A dermoscopic image of a skin lesion.
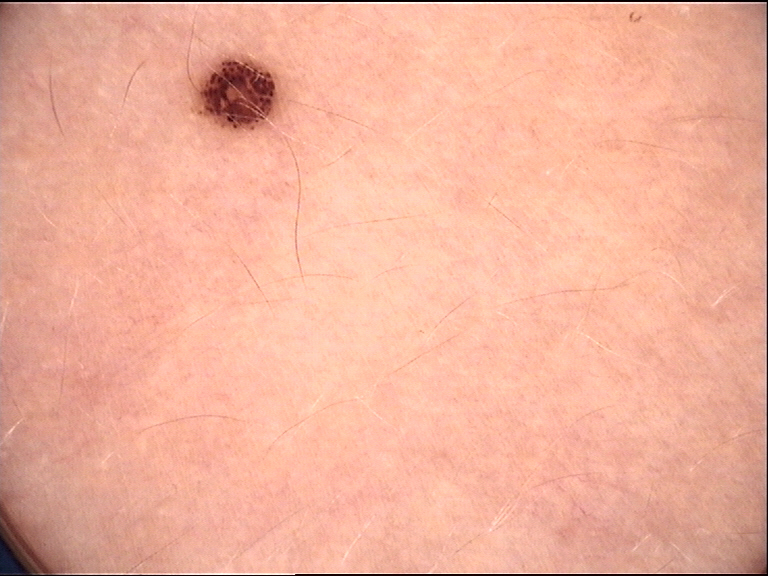Consistent with a dysplastic junctional nevus.